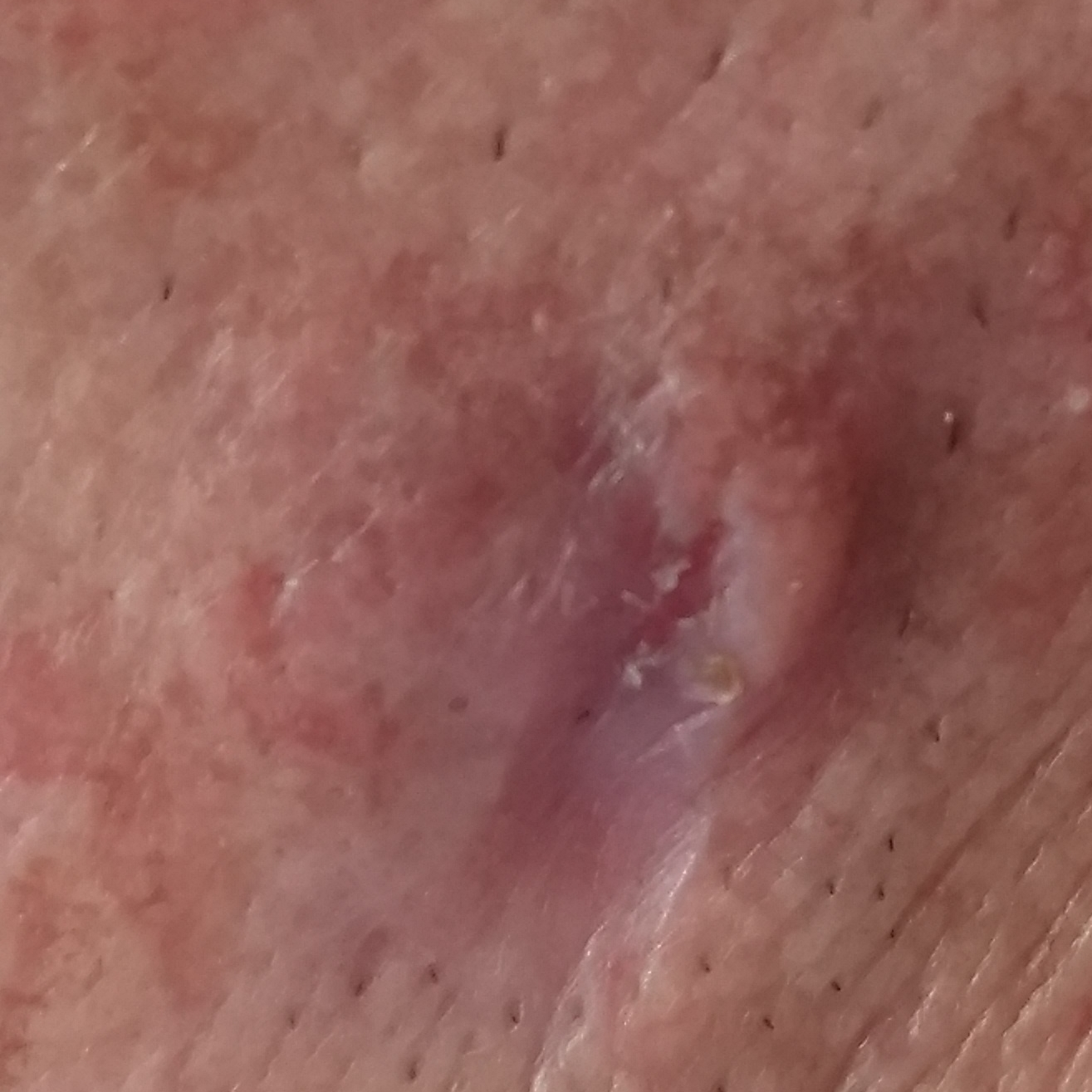Patient and lesion: A clinical close-up photograph of a skin lesion. By history, pesticide exposure. Fitzpatrick phototype II. The lesion involves an ear. The lesion measures approximately 7 × 5 mm. By the patient's account, the lesion itches, has bled, has grown, and is elevated. Conclusion: The biopsy diagnosis was a malignant skin lesion — a squamous cell carcinoma.